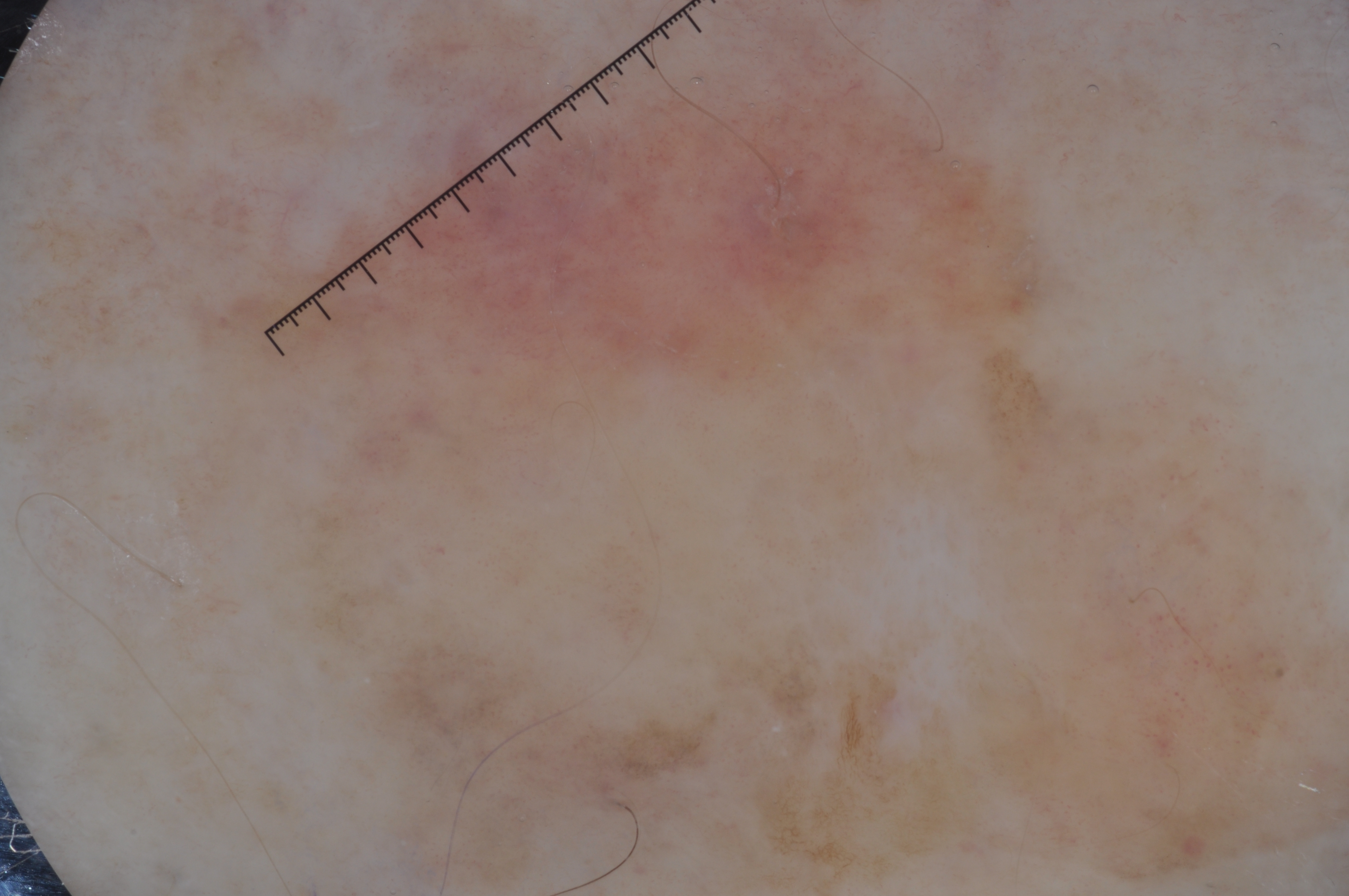{
  "patient": {
    "sex": "female",
    "age_approx": 75
  },
  "image": {
    "modality": "dermoscopy"
  },
  "lesion_location": "spans the dermoscopic field",
  "dermoscopic_features": {
    "present": [
      "pigment network",
      "milia-like cysts",
      "negative network"
    ],
    "absent": [
      "streaks"
    ]
  },
  "diagnosis": {
    "name": "seborrheic keratosis",
    "malignancy": "benign",
    "lineage": "keratinocytic",
    "provenance": "clinical"
  }
}